A macroscopic clinical photograph of a skin lesion. Imaged for a research study, with no referral diagnosis recorded. The patient says their skin tans without first burning:
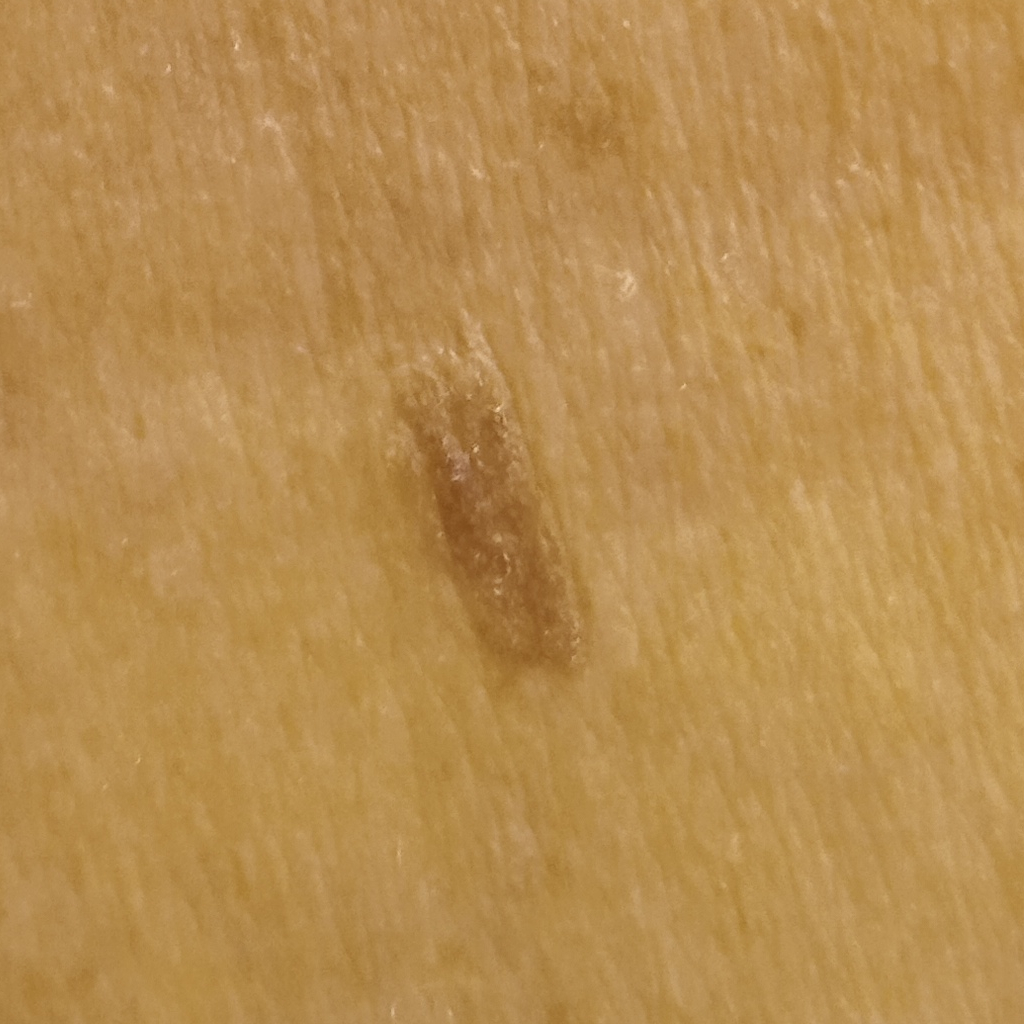Q: Where is the lesion?
A: the back
Q: What was the diagnosis?
A: seborrheic keratosis (dermatologist consensus)